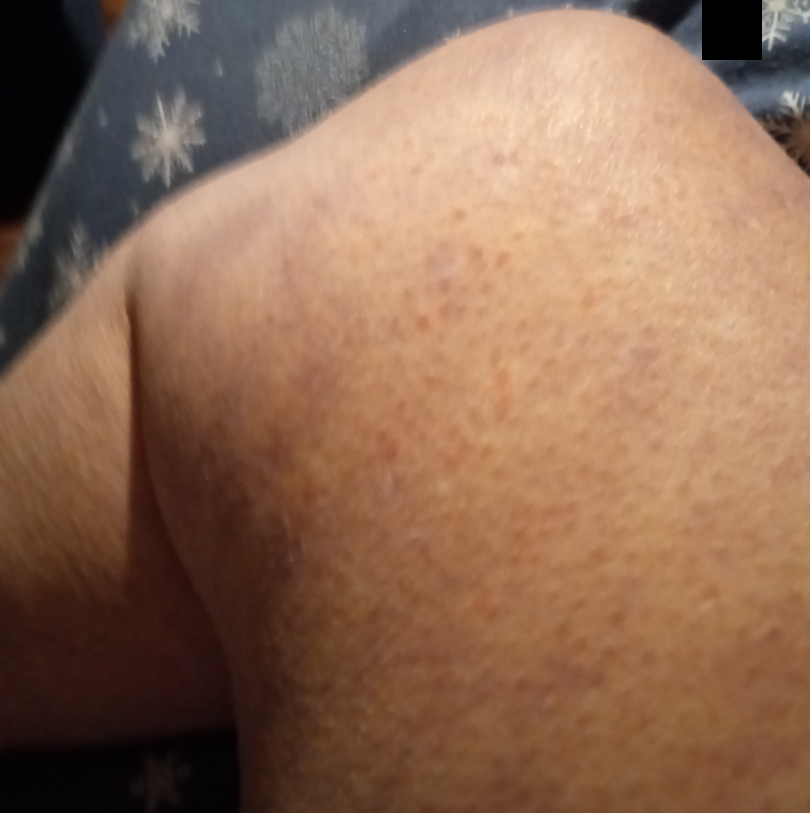Notes:
- assessment · indeterminate from the photograph
- photo taken · at a distance
- subject · female
- self-categorized as · a rash
- systemic symptoms · none reported
- lesion texture · raised or bumpy
- lesion symptoms · burning and itching
- anatomic site · leg, arm and back of the hand